The contributor is a female aged 70–79, the affected area is the head or neck and arm, texture is reported as raised or bumpy, present for about one day, self-categorized by the patient as a rash, no relevant systemic symptoms, the photo was captured at an angle:
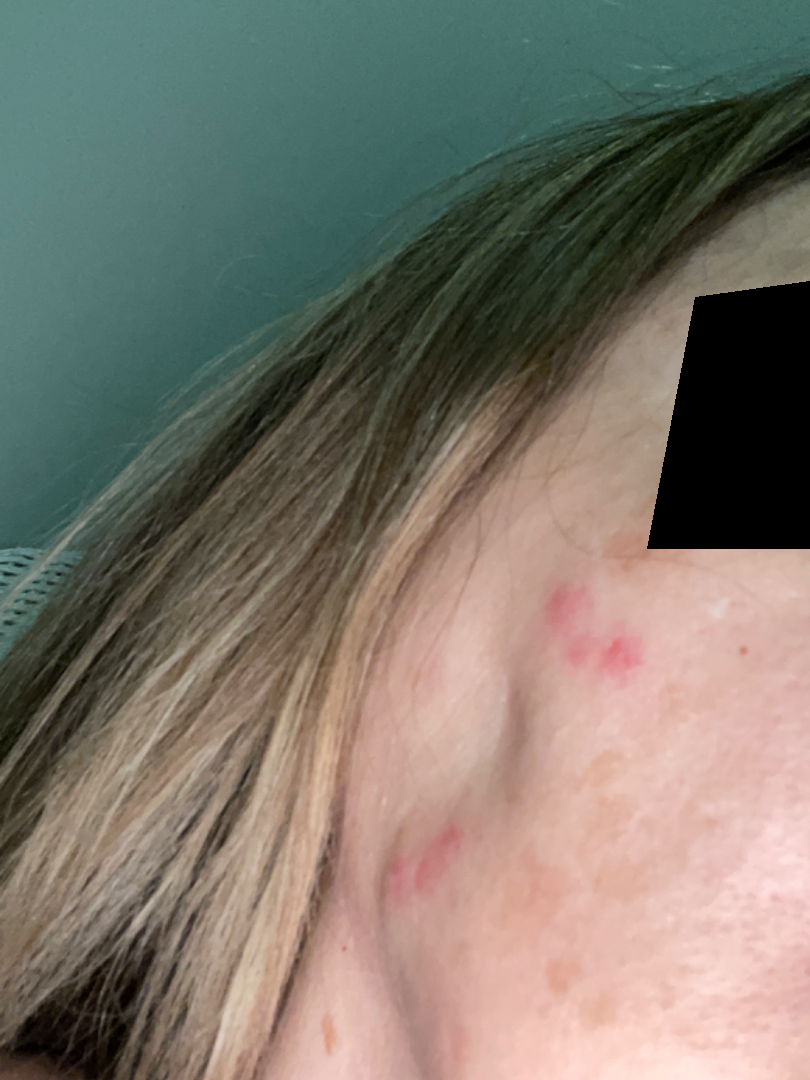No differential diagnosis could be assigned on photographic review.